The patient is a male roughly 60 years of age, a dermoscopic close-up of a skin lesion — 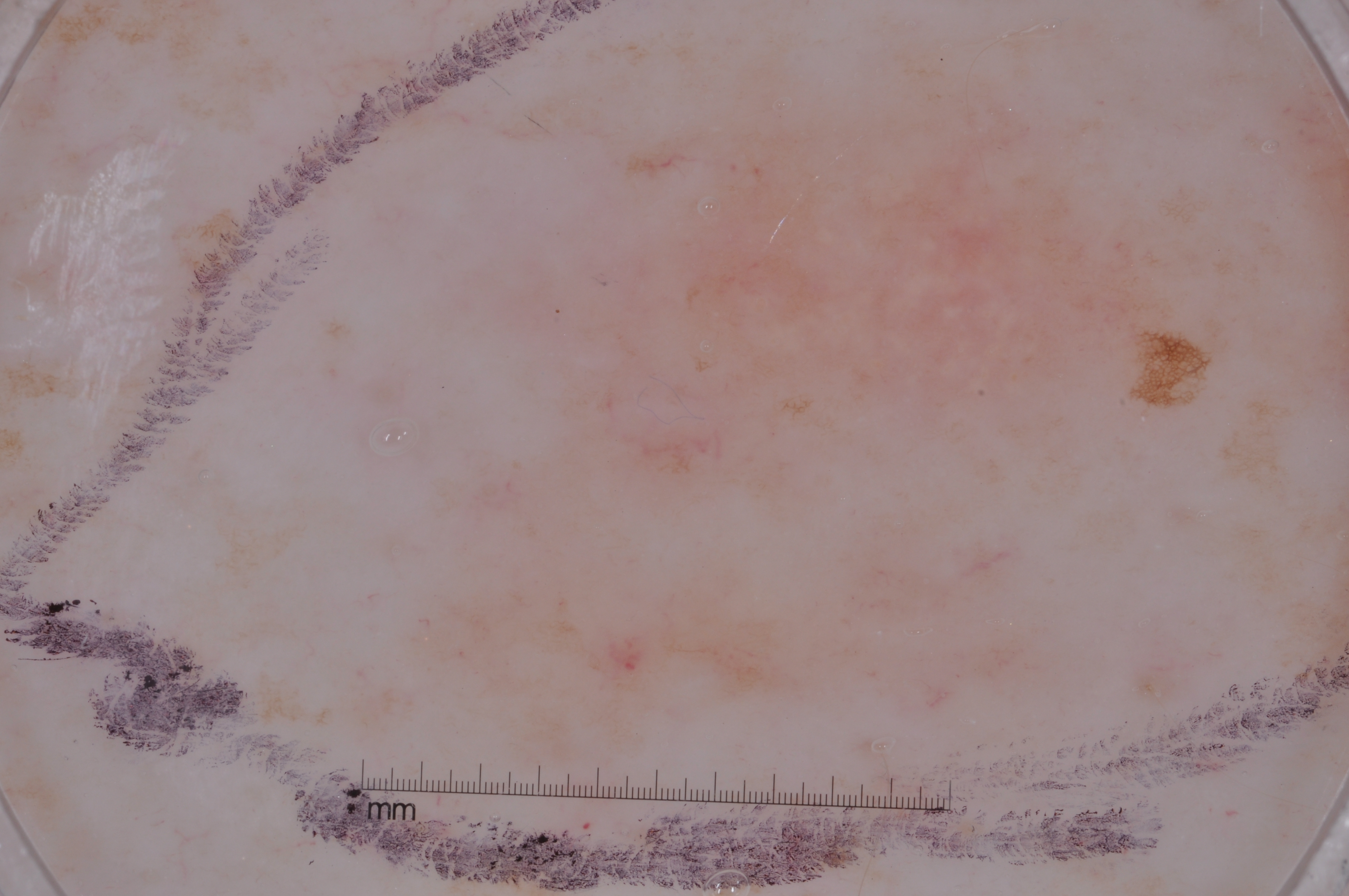A large lesion occupying much of the field.
Dermoscopically, the lesion shows pigment network, with no negative network, milia-like cysts, or streaks.
With coordinates (x1, y1, x2, y2), the lesion spans 285, 12, 1298, 797.
Diagnosed as a melanocytic nevus, a benign lesion.